A dermatoscopic image of a skin lesion:
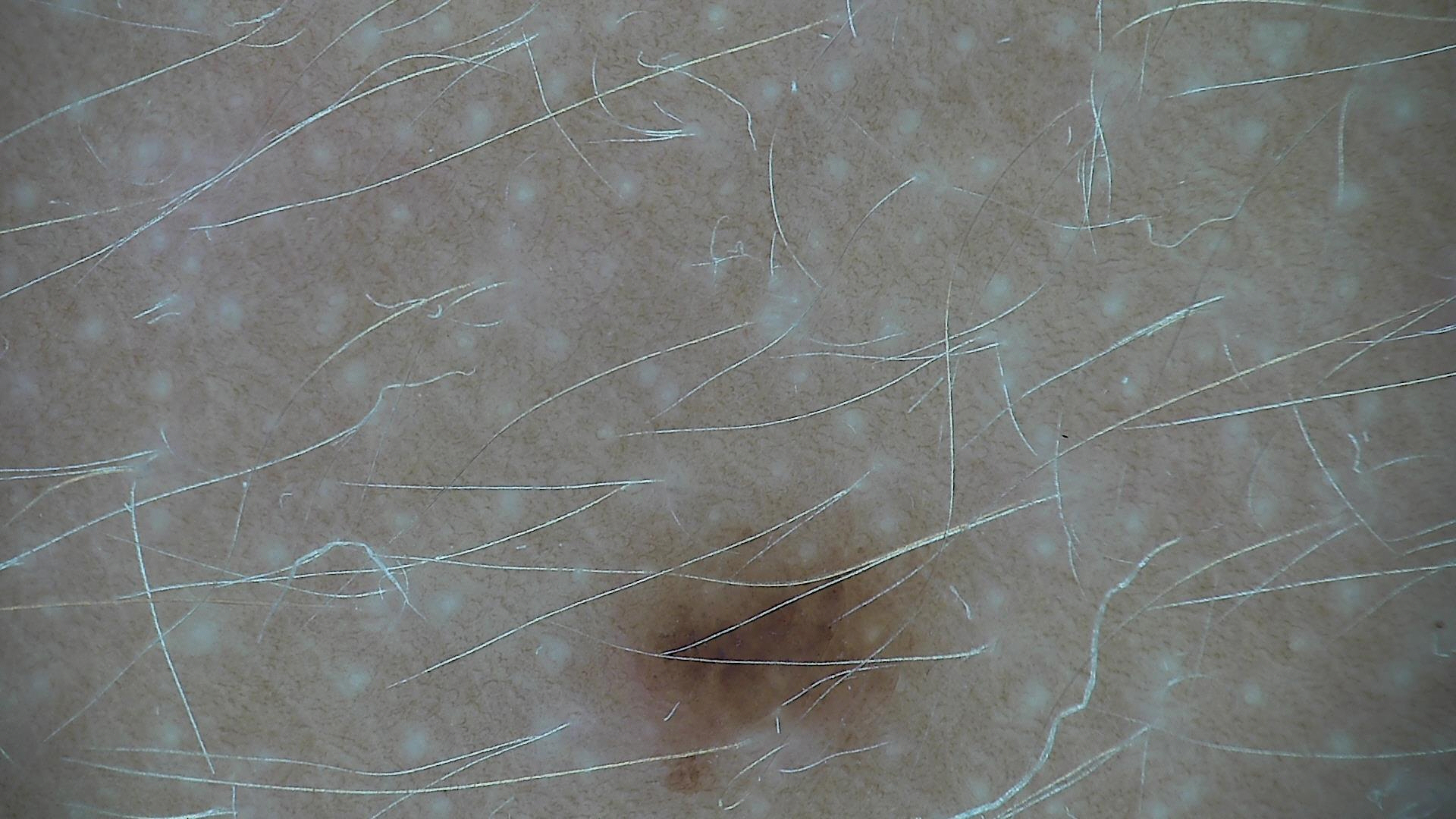Classified as a dysplastic junctional nevus.